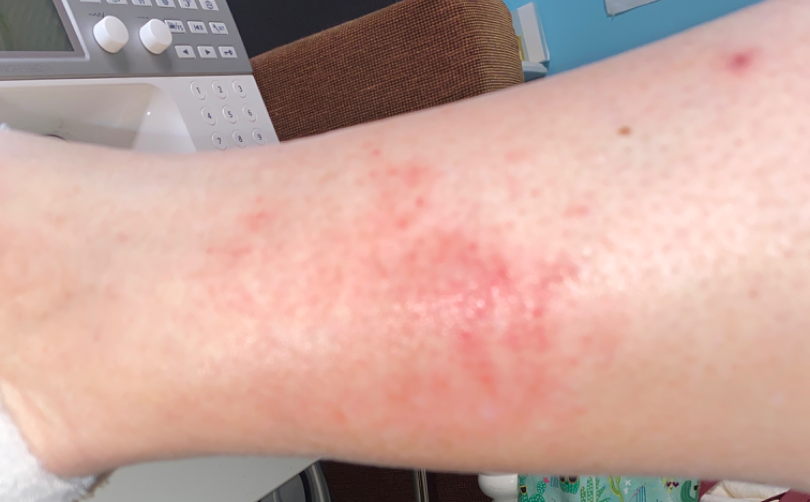No differential diagnosis could be assigned on photographic review.
The affected area is the leg.
The photo was captured at a distance.